The contributor is 60–69, female; located on the leg and arm; this is a close-up image:
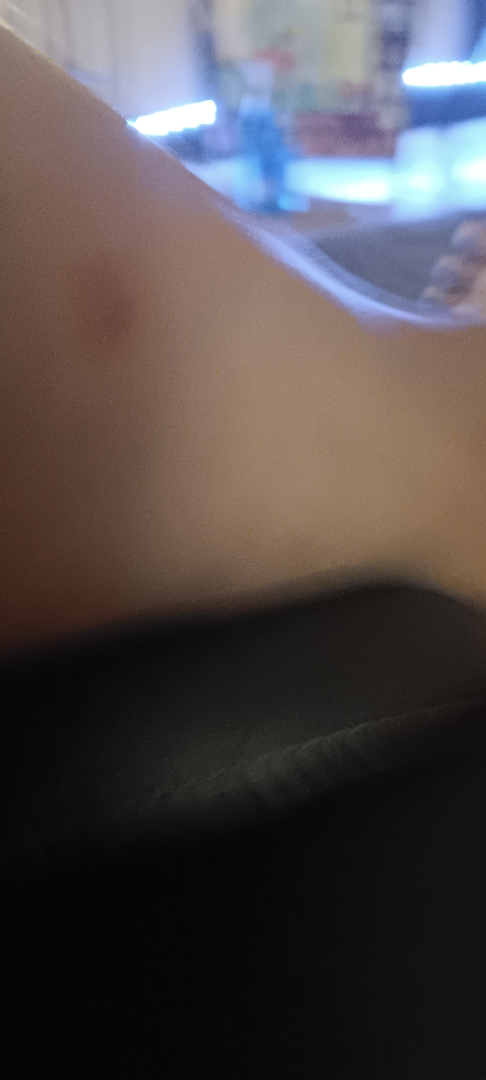assessment: indeterminate from the photograph